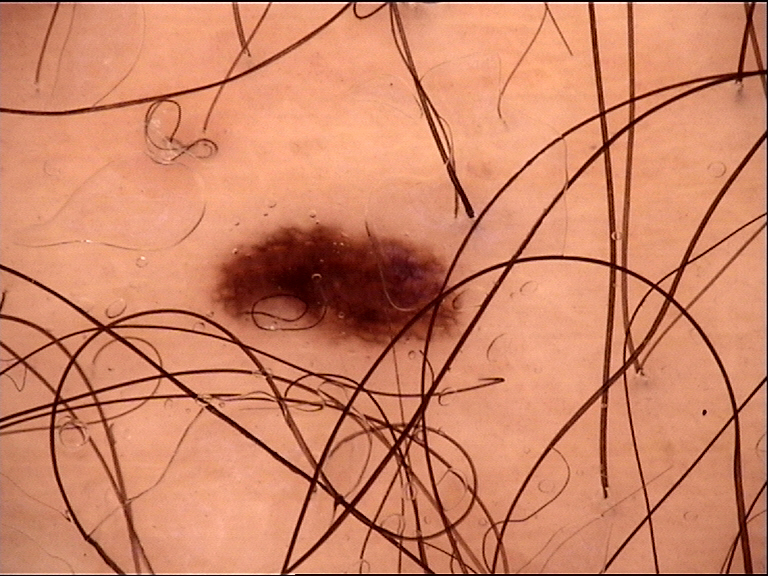Summary: Dermoscopy of a skin lesion. This is a banal lesion. Conclusion: Diagnosed as a junctional nevus.